A patient aged 35 — 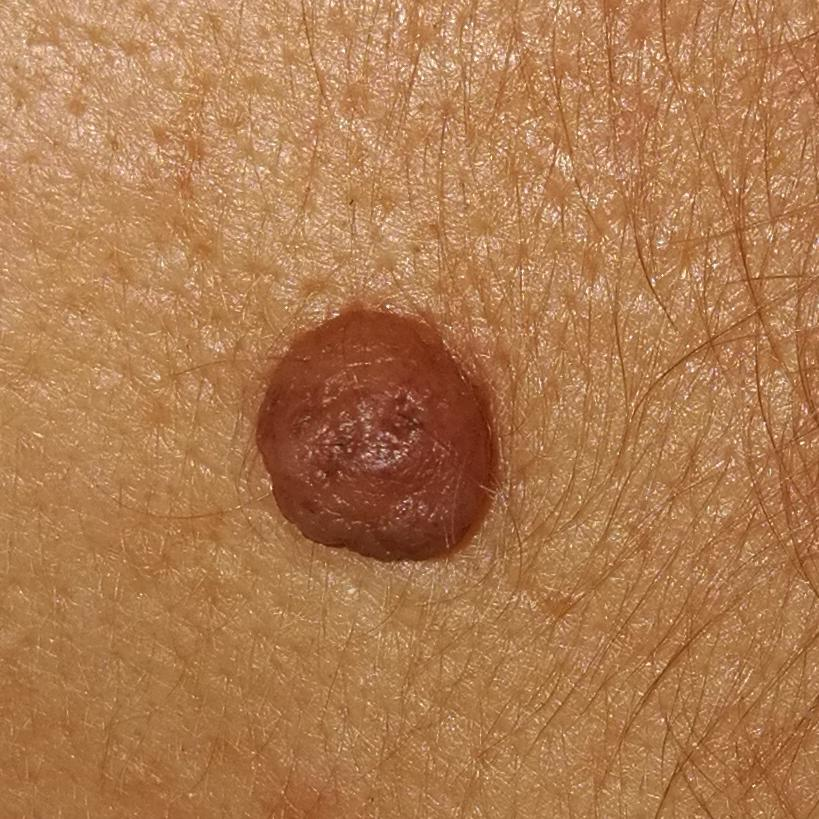  lesion_location: the face
  diagnosis:
    name: nevus
    code: NEV
    malignancy: benign
    confirmation: clinical consensus